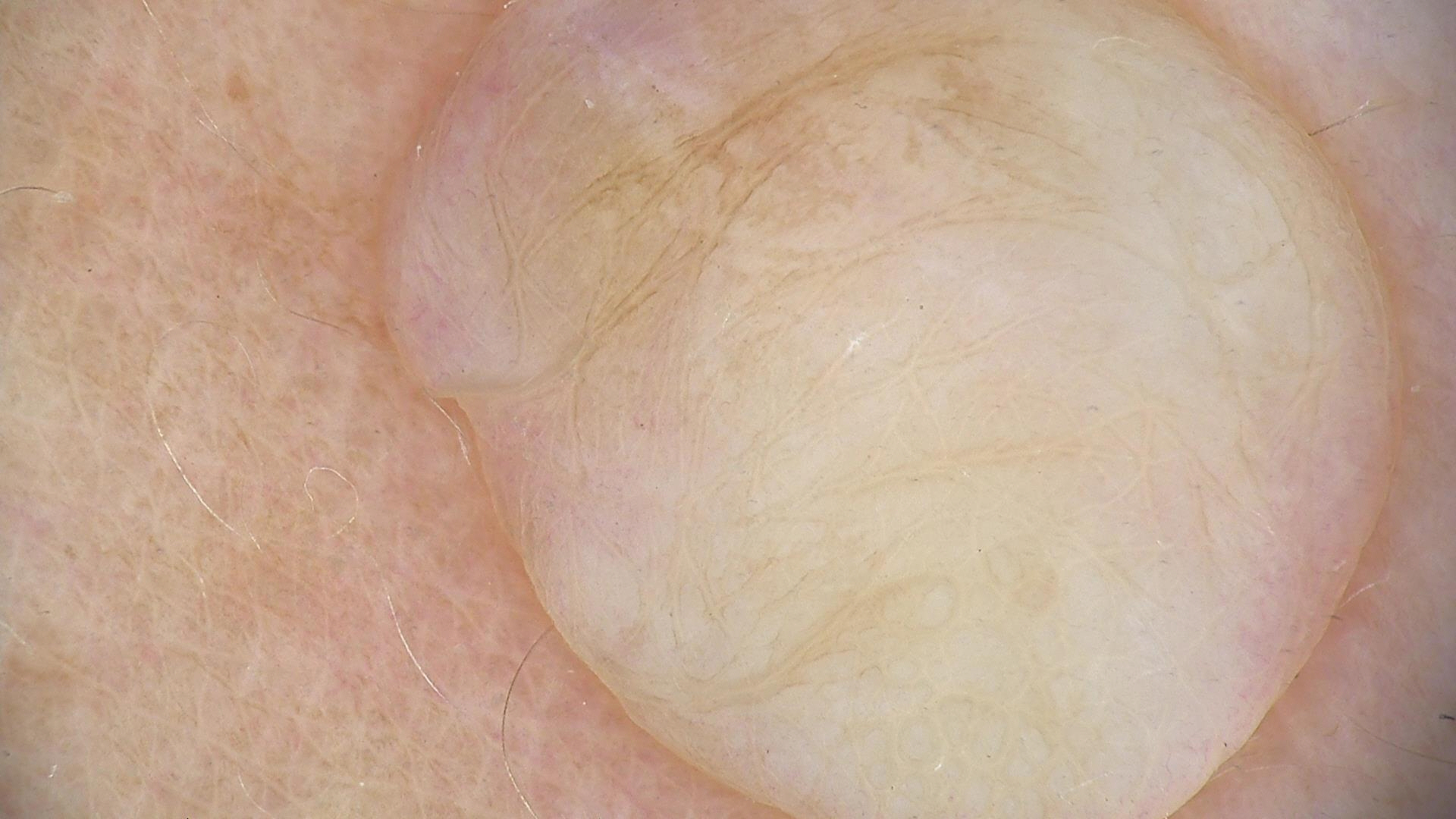modality: dermoscopy, label: dermal nevus (expert consensus).